Located on the head or neck. The patient indicates the lesion is fluid-filled. The lesion is associated with pain and itching. No associated systemic symptoms reported. The photo was captured at an angle. Self-categorized by the patient as a rash. Present for less than one week: 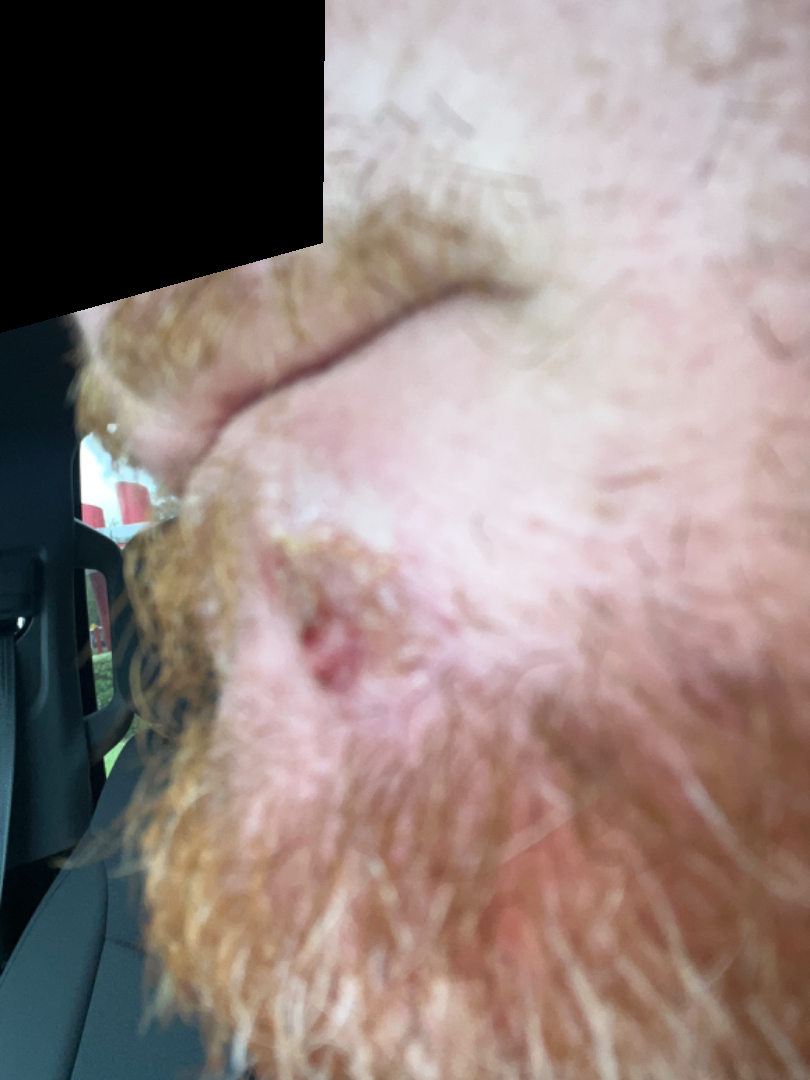Findings:
• dermatologist impression: favoring Impetigo; the differential also includes Infected eczema; less likely is Seborrheic Dermatitis